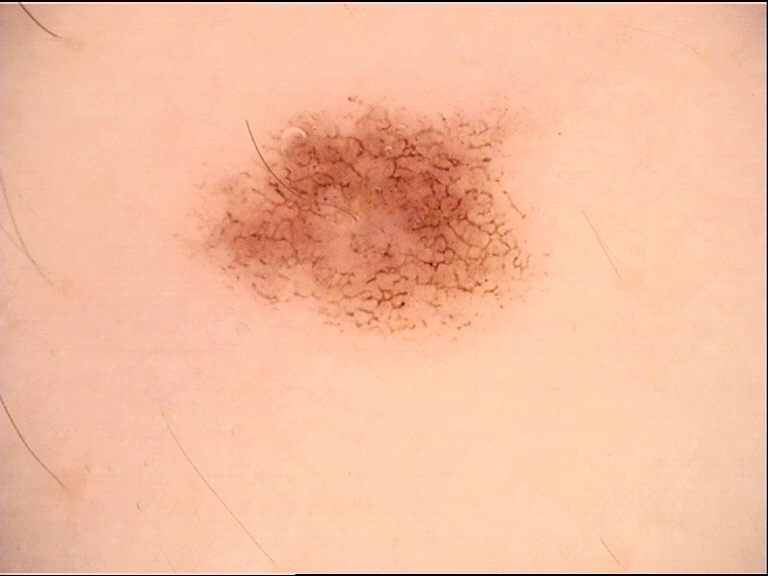Consistent with a dysplastic junctional nevus.